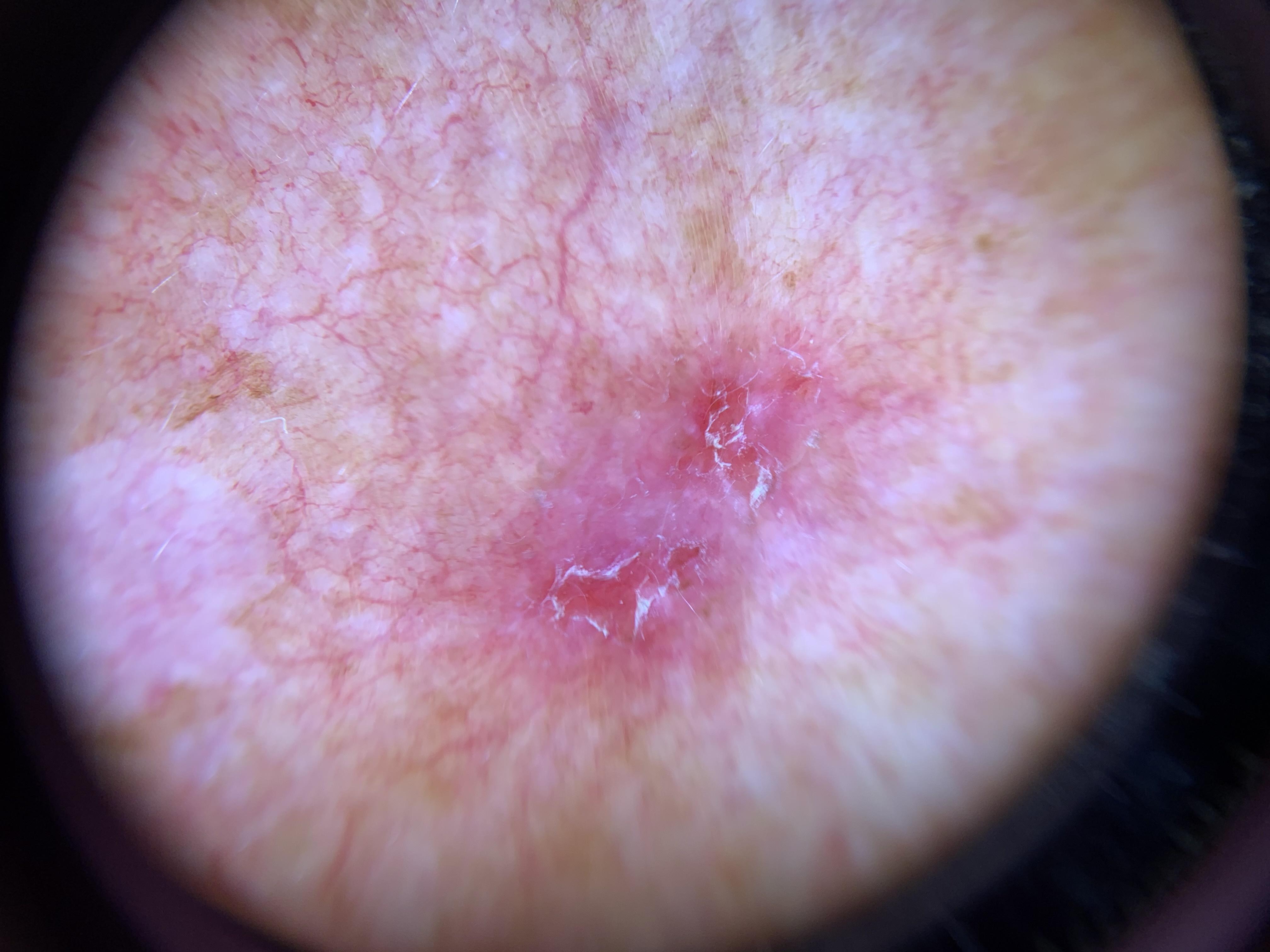diagnosis=Basal cell carcinoma (biopsy-proven)